A dermoscopy image of a single skin lesion.
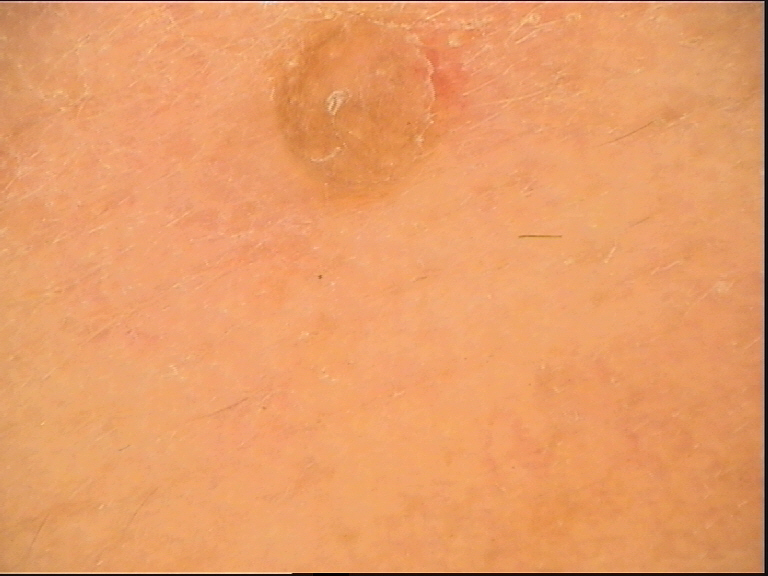The morphology is that of a keratinocytic lesion.
Consistent with a benign lesion — a seborrheic keratosis.